A female patient 71 years old. Imaged for a research study, with no referral diagnosis recorded. The patient reports a personal history of skin cancer, a personal history of cancer, no sunbed use, and no prior organ transplant. The patient says their skin reddens with sun exposure. The patient describes having few moles overall: 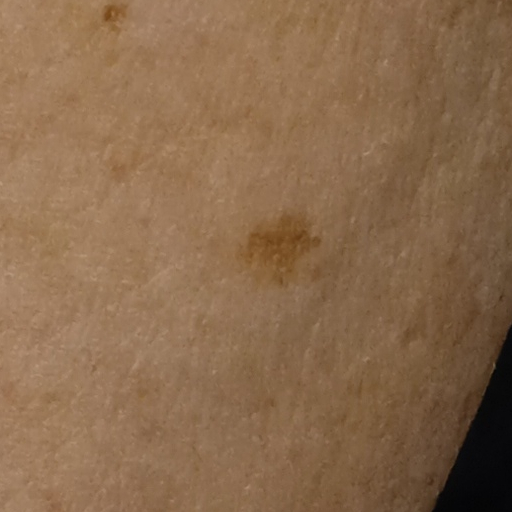The lesion is located on an arm. The lesion measures approximately 6.1 mm. Dermatologist review favored a melanocytic nevus.